The photo was captured at an angle · the affected area is the leg: 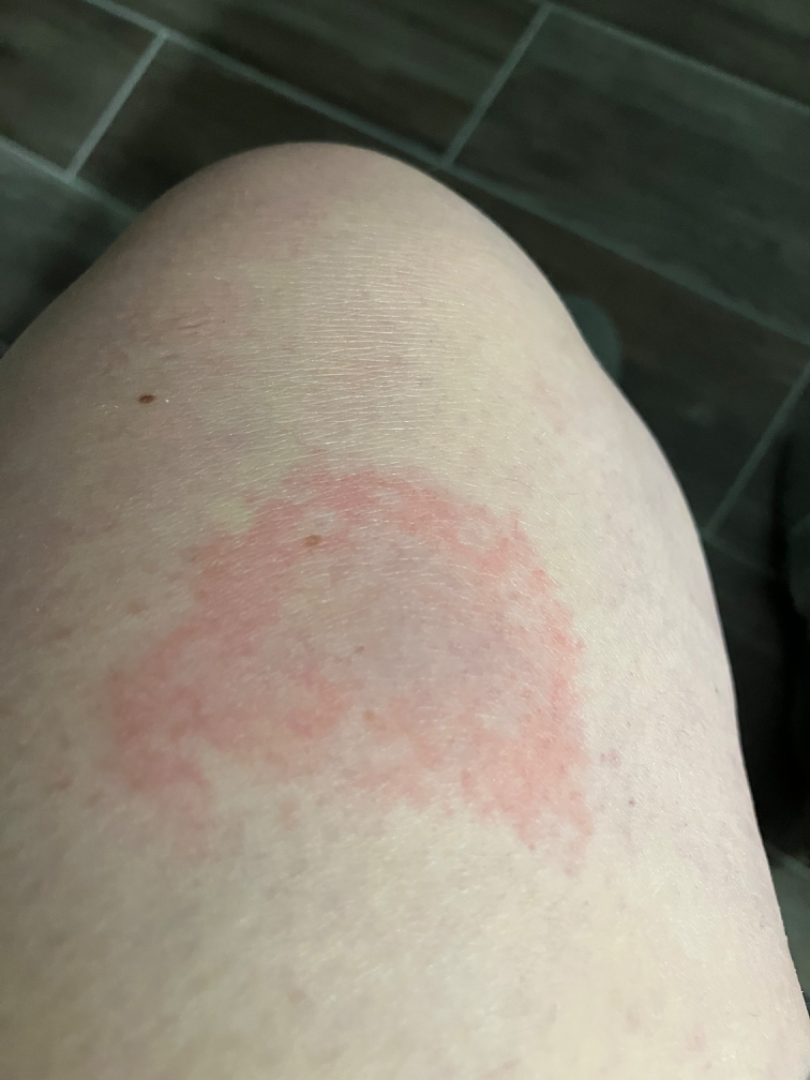duration: less than one week
texture: raised or bumpy
differential:
  tied_lead:
    - Allergic Contact Dermatitis
    - Erythema migrans